The patient also reports shortness of breath · the patient is a female aged 50–59 · this image was taken at an angle · the lesion involves the head or neck · the patient reports pain and itching · the patient reports the condition has been present for less than one week · the patient considered this a rash · texture is reported as rough or flaky and raised or bumpy — 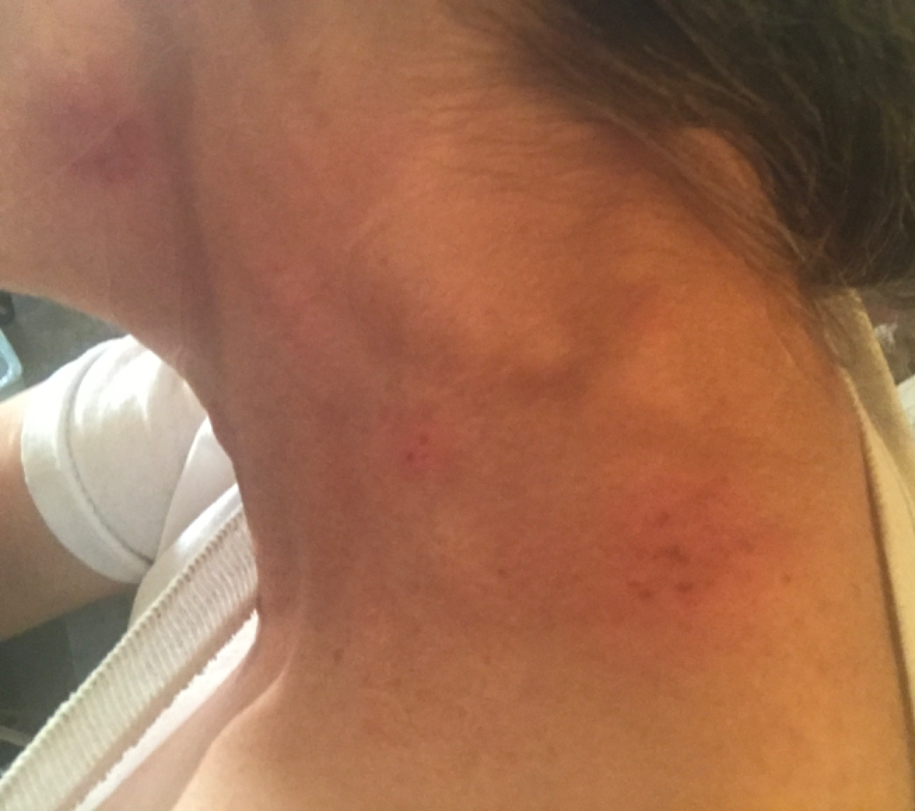The condition could not be reliably identified from the image.